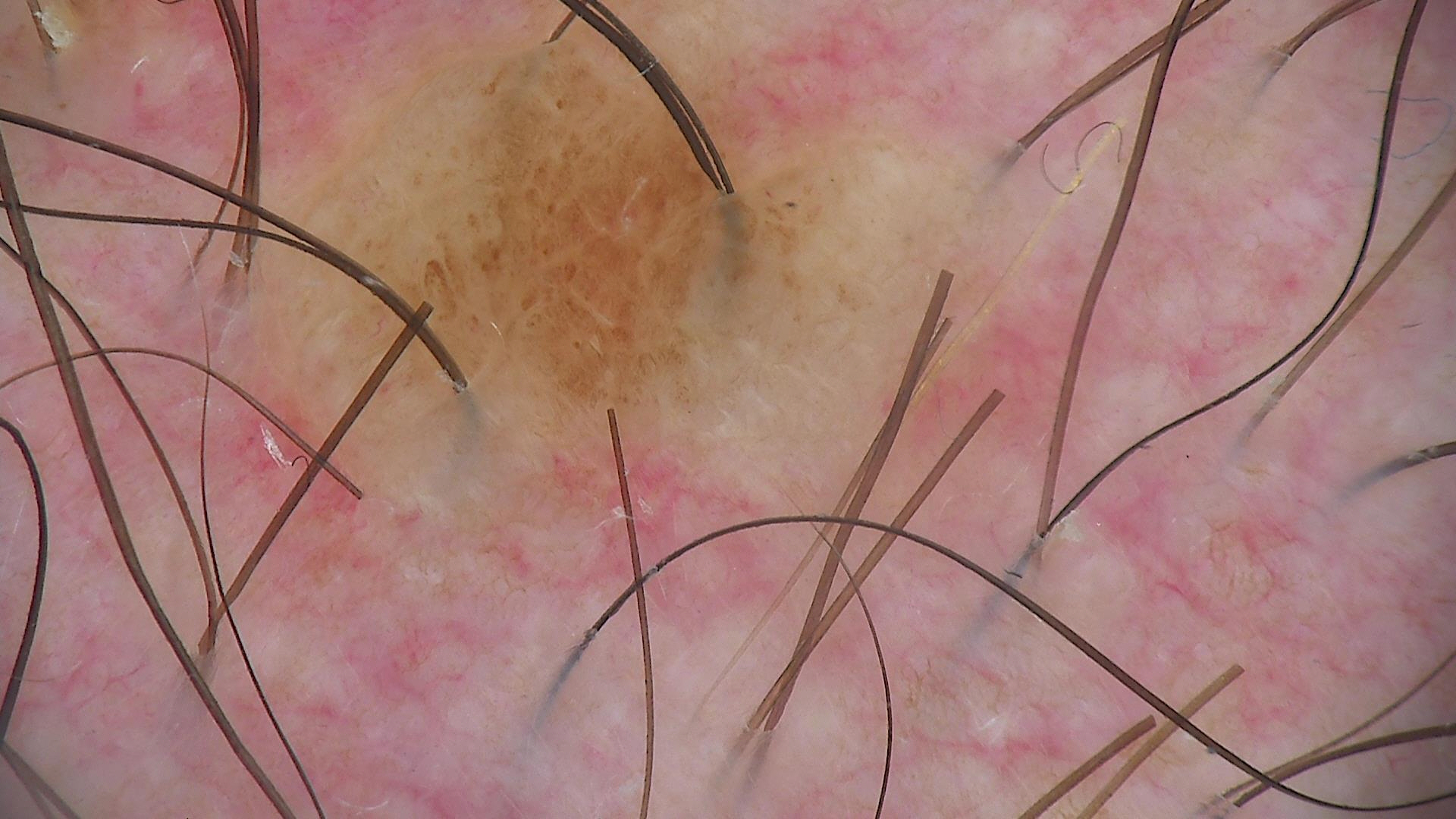Findings:
• image type — dermatoscopy
• diagnostic label — compound nevus (expert consensus)